Dermoscopy of a skin lesion:
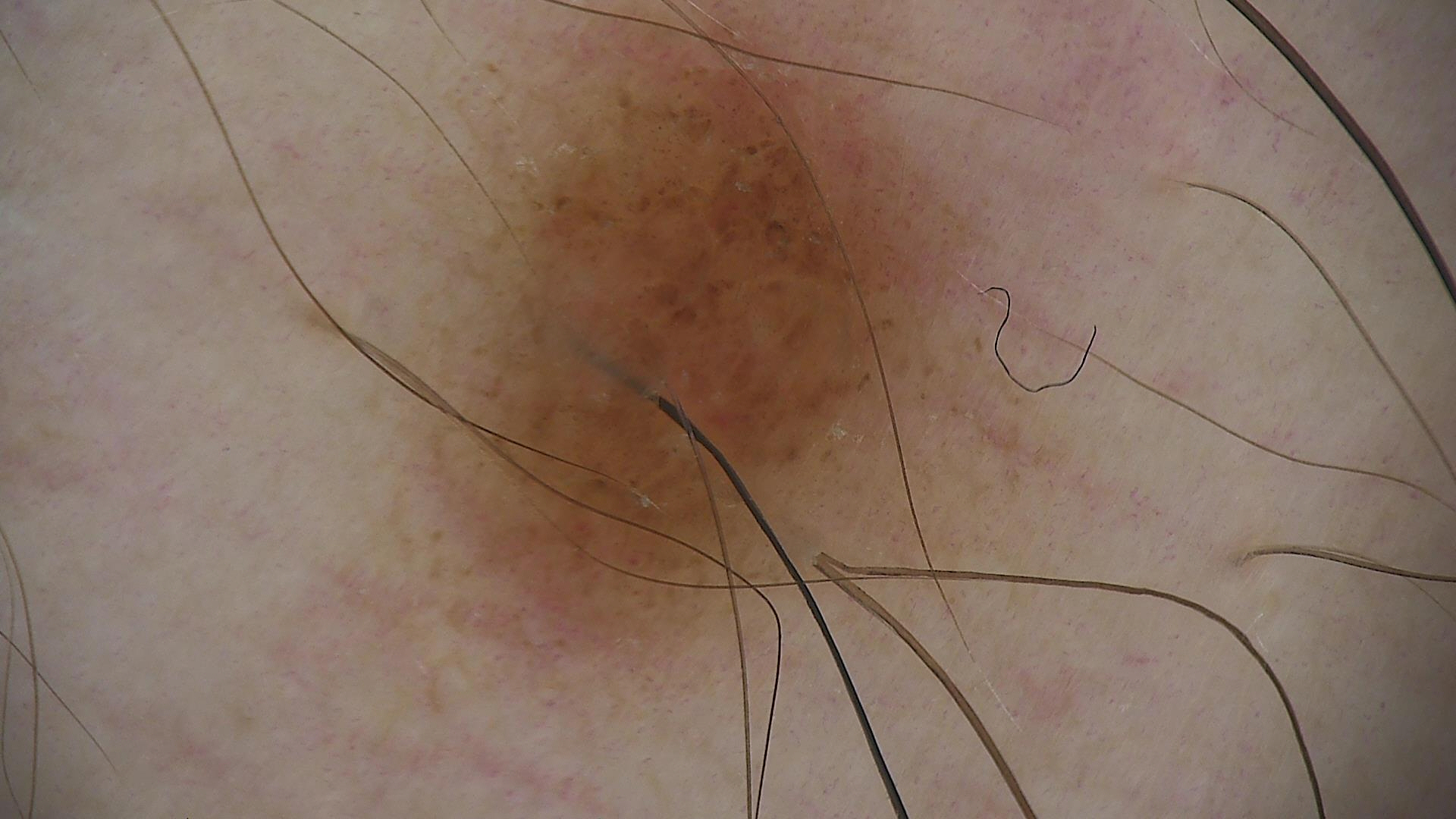Findings:
– assessment — compound nevus (expert consensus)